The lesion involves the arm, this is a close-up image:
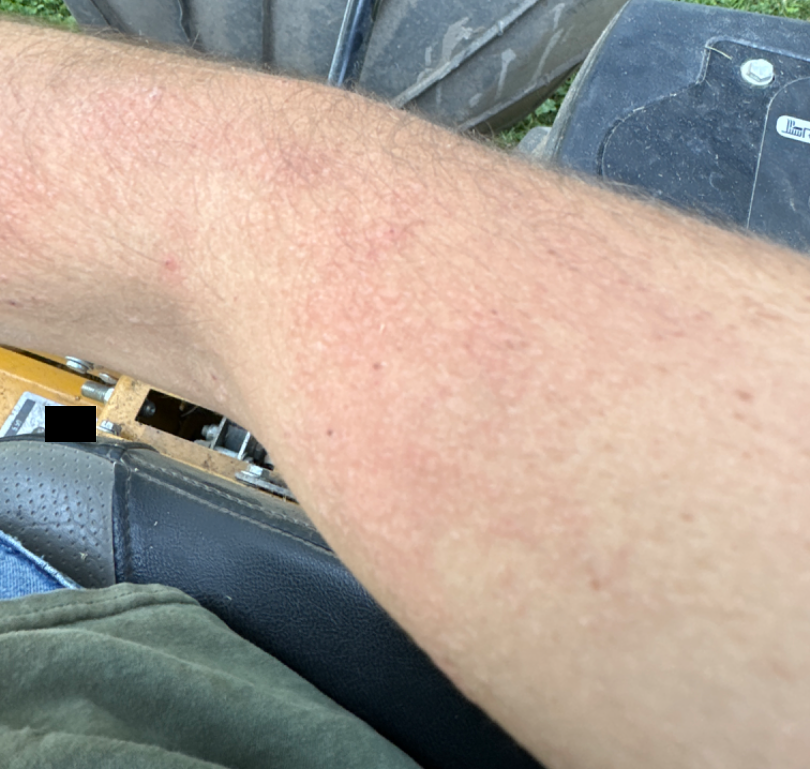The patient considered this a rash. No constitutional symptoms were reported. The lesion is associated with enlargement and itching. Texture is reported as rough or flaky. The condition has been present for less than one week. Eczema, Allergic Contact Dermatitis and Irritant Contact Dermatitis were considered with similar weight.